Reported duration is about one day · the photo was captured at a distance · the subject is 18–29, female · the affected area is the back of the torso · texture is reported as rough or flaky and raised or bumpy:
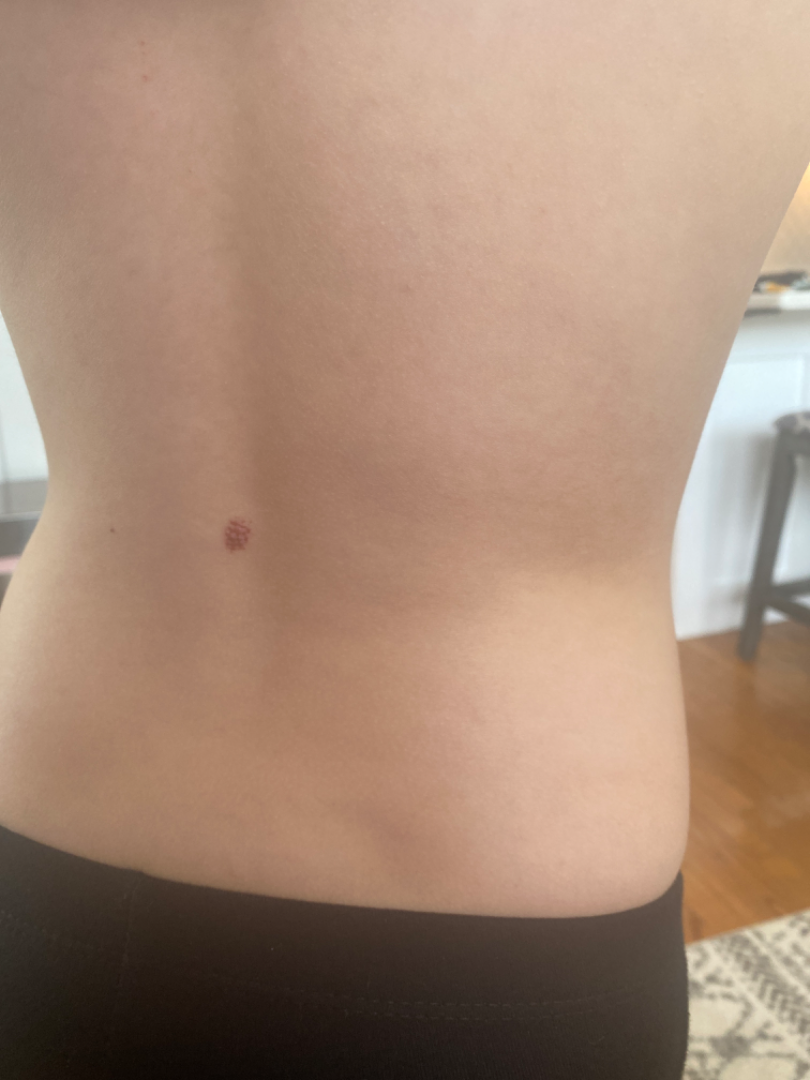* assessment · unable to determine